A dermoscopic image of a skin lesion:
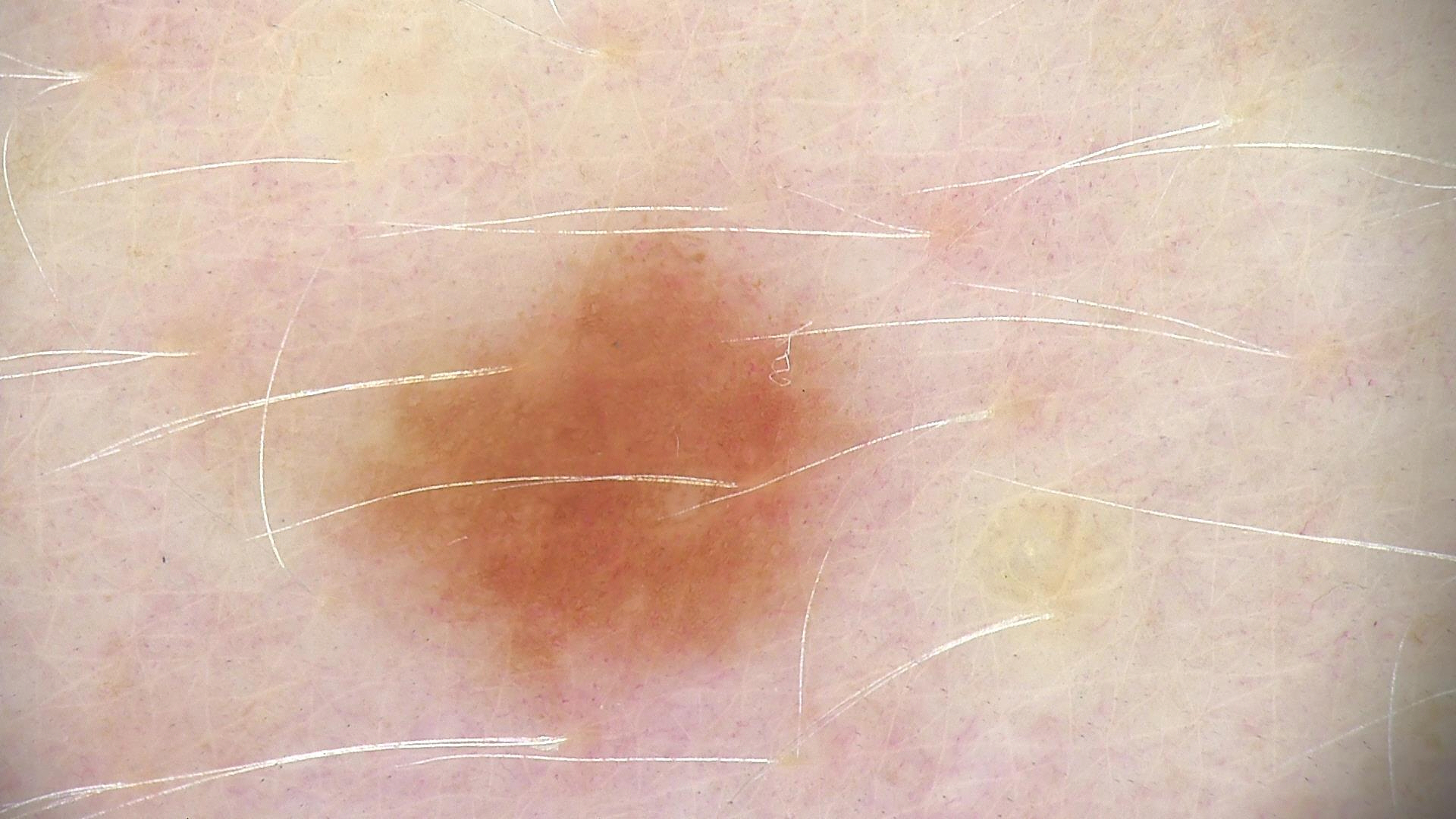| feature | finding |
|---|---|
| classification | banal |
| label | junctional nevus (expert consensus) |